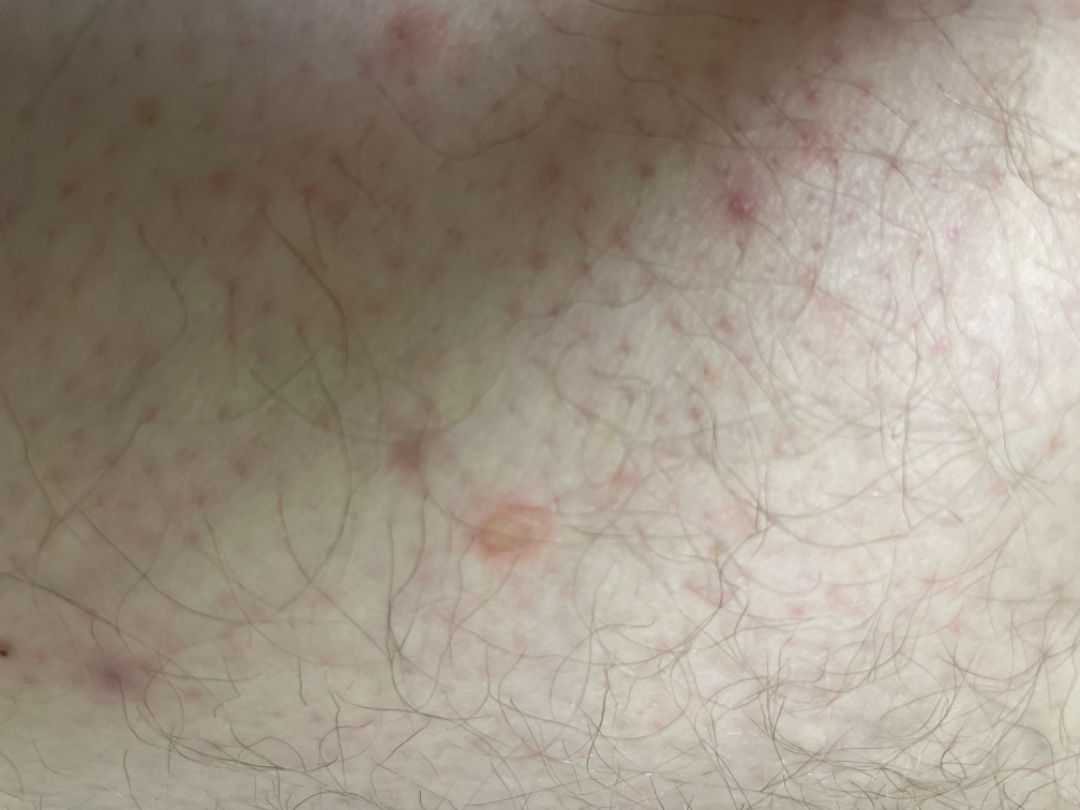The case was indeterminate on photographic review. Located on the leg. Texture is reported as raised or bumpy and fluid-filled. The photograph is a close-up of the affected area. Skin tone: Fitzpatrick phototype III; lay reviewers estimated Monk skin tone scale 2. Reported duration is less than one week.